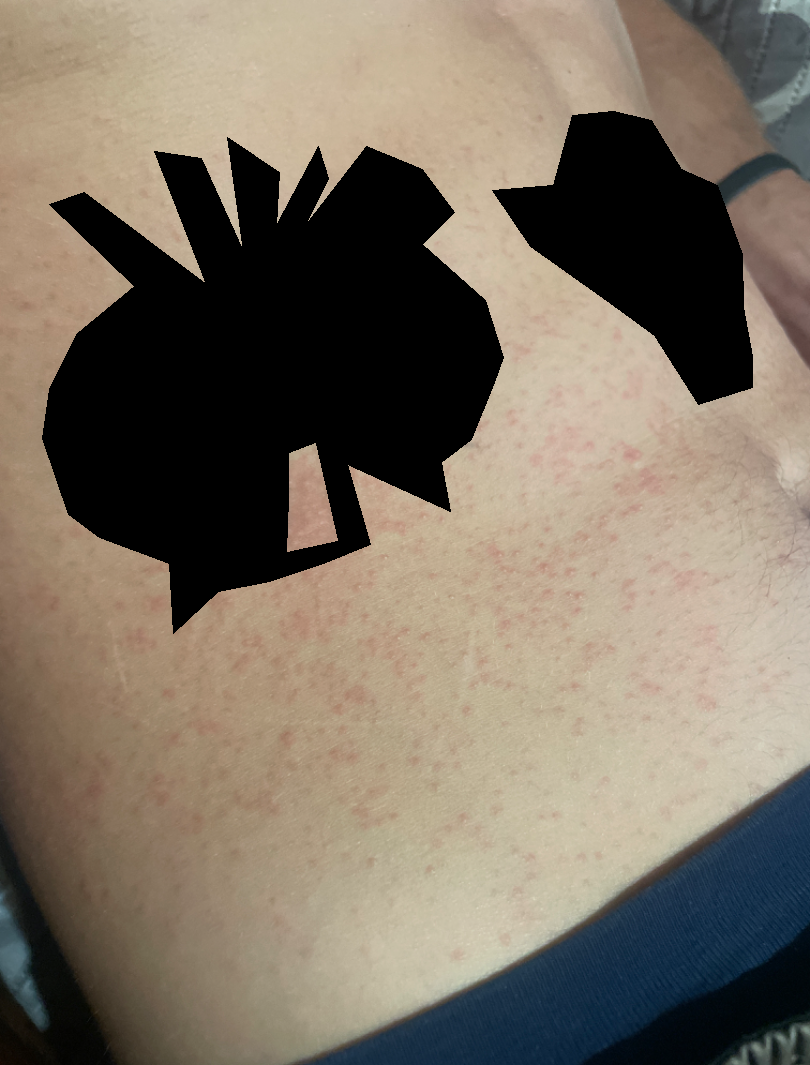{"shot_type": "close-up", "body_site": "front of the torso", "differential": {"tied_lead": ["Drug Rash", "Viral Exanthem"], "unlikely": ["Miliaria"]}}